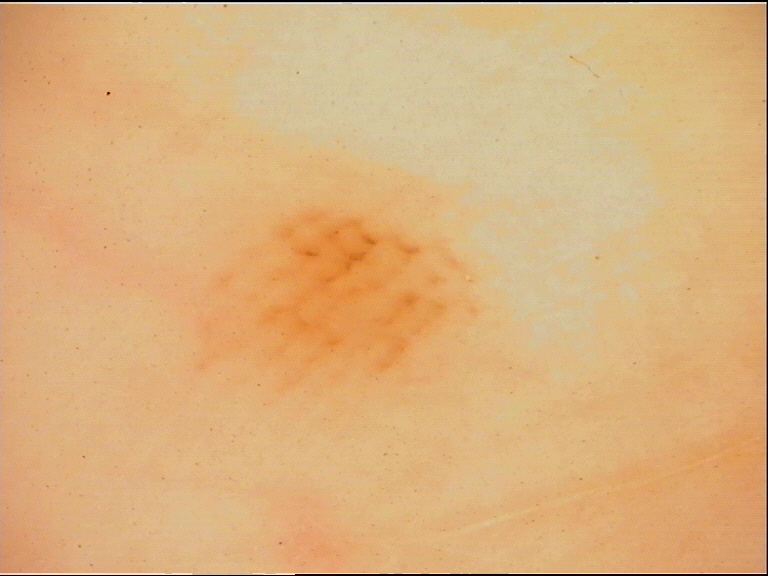{
  "image": "dermatoscopy",
  "diagnosis": {
    "name": "acral junctional nevus",
    "code": "ajb",
    "malignancy": "benign",
    "super_class": "melanocytic",
    "confirmation": "expert consensus"
  }
}